A male patient aged around 70. A skin lesion imaged with contact-polarized dermoscopy. The patient was assessed as skin type II — 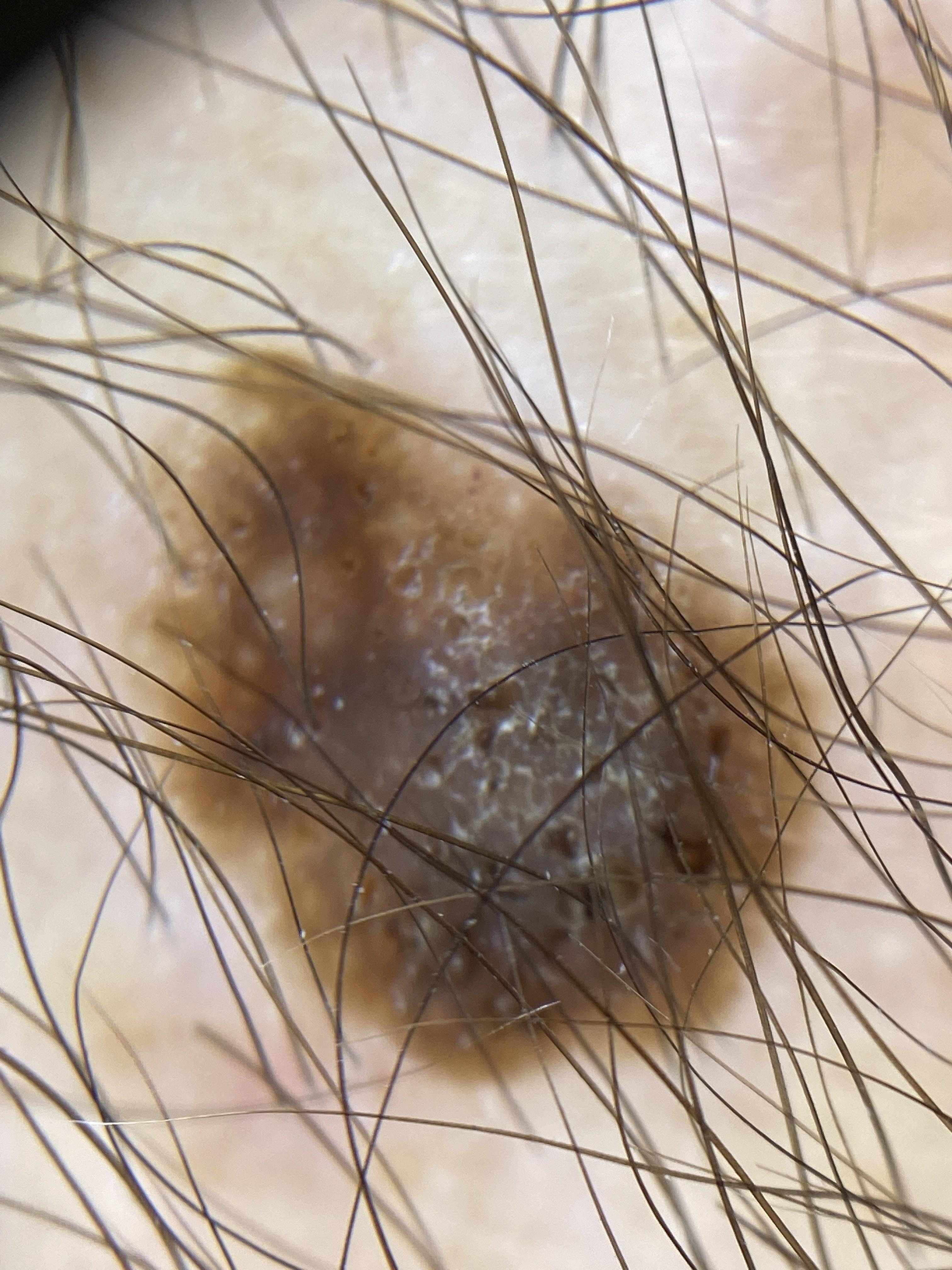site: an upper extremity
diagnosis: Seborrheic keratosis (clinical impression)